A dermoscopic close-up of a skin lesion: 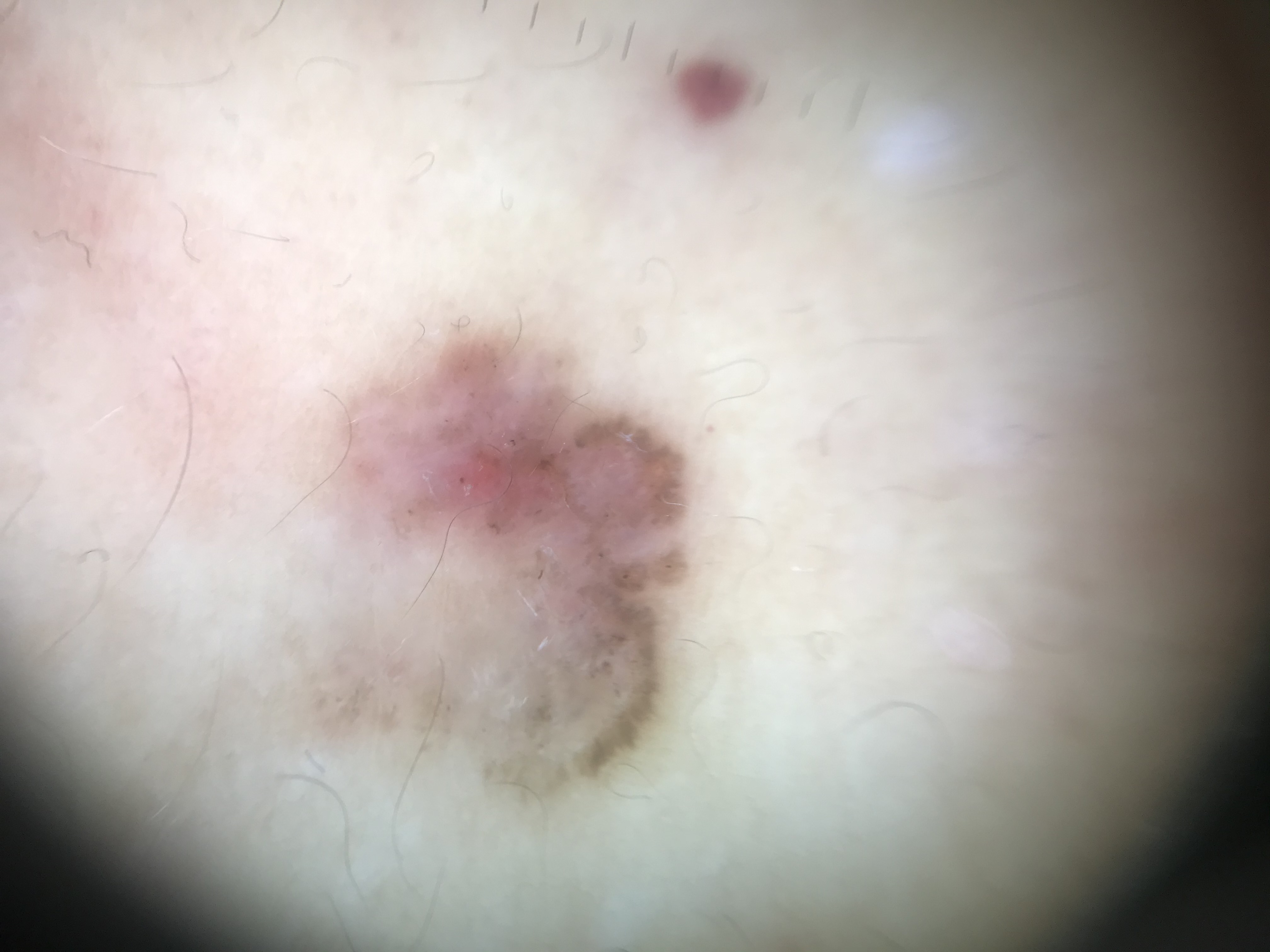category = keratinocytic, class = basal cell carcinoma (biopsy-proven).